A dermoscopic image of a skin lesion: 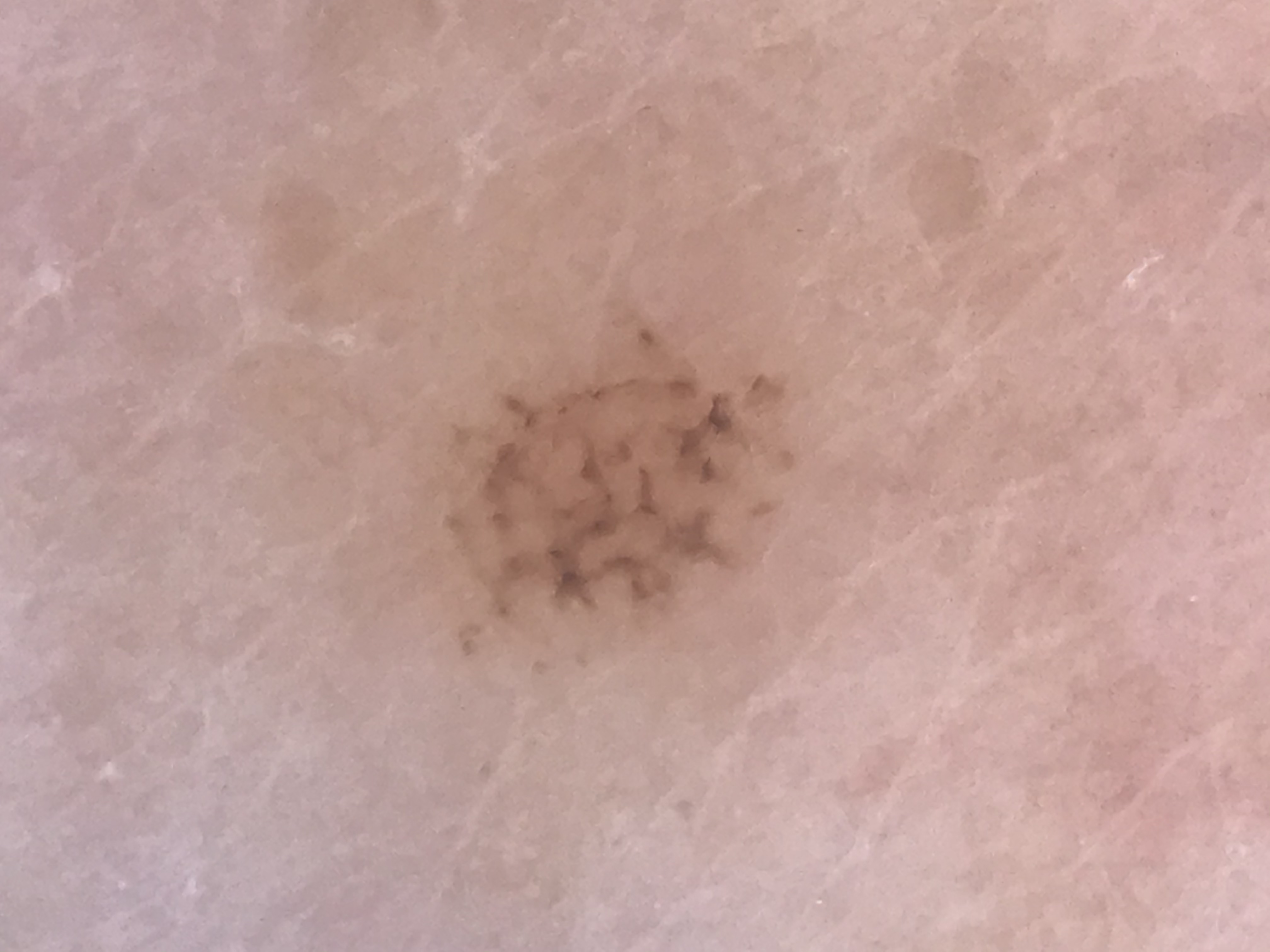assessment: acral dysplastic junctional nevus (expert consensus).